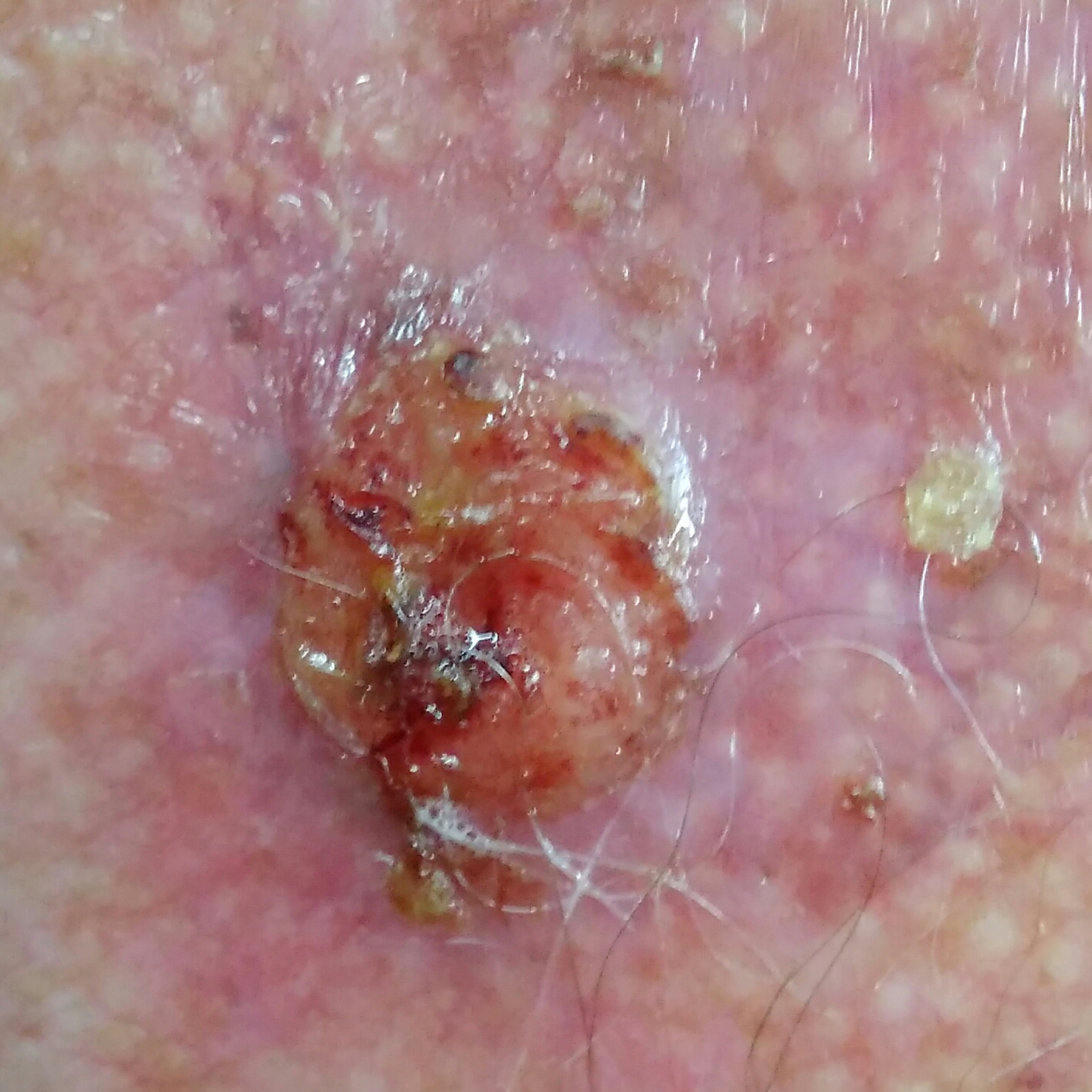Findings:
A male subject age 70. Recorded as Fitzpatrick skin type II. The chart notes alcohol use, no pesticide exposure, and no prior malignancy (patient or family). A clinical photograph showing a skin lesion. The lesion is on the chest. Measuring about 18 × 13 mm. The patient describes that the lesion has grown and is elevated, but does not hurt.
Diagnosis:
Histopathology confirmed a malignant lesion — a squamous cell carcinoma.